A dermoscopic photograph of a skin lesion.
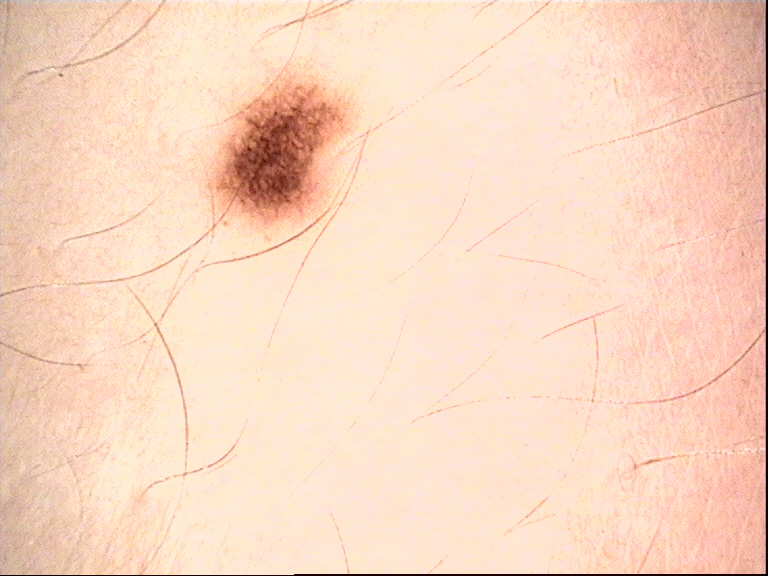diagnosis: dysplastic junctional nevus (expert consensus).